A patient in their mid-40s; a clinical photo of a skin lesion taken with a smartphone — 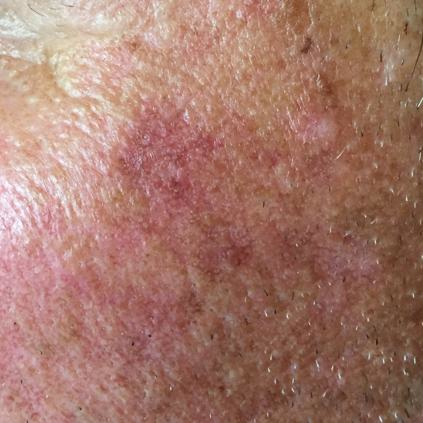site = the face | symptoms = itching / no pain, no change in appearance | diagnostic label = actinic keratosis (clinical consensus).